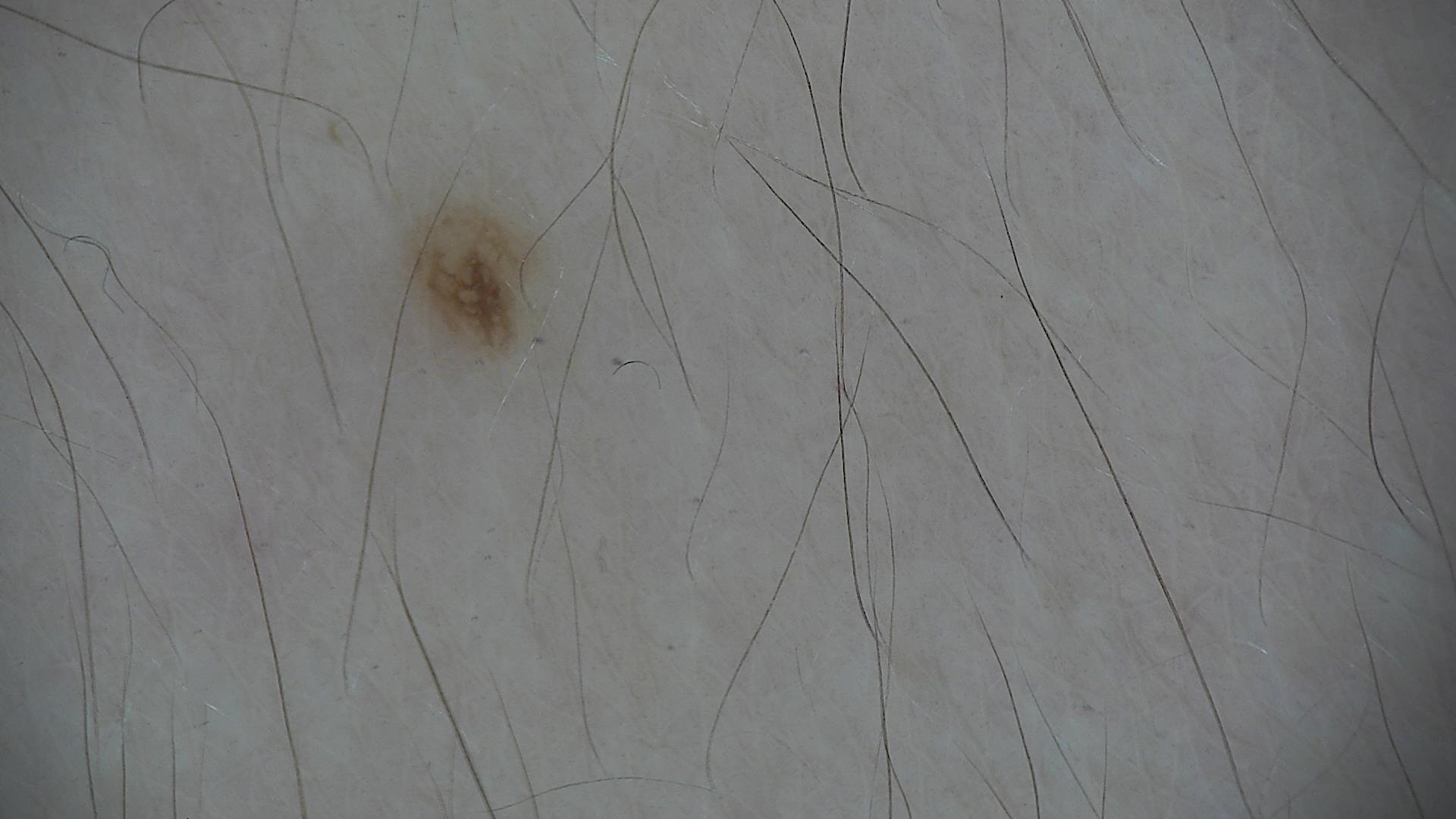Case: A dermoscopic photograph of a skin lesion. Impression: The diagnosis was a banal lesion — a junctional nevus.